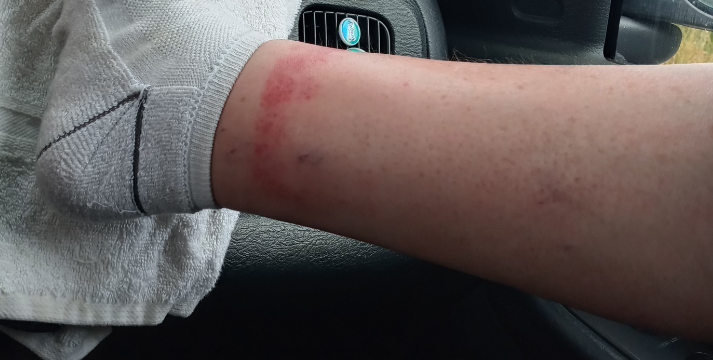Clinical context:
The affected area is the leg. The photo was captured at a distance.
Assessment:
On photographic review, Contact dermatitis and Allergic Contact Dermatitis were considered with similar weight; a more distant consideration is Stasis Dermatitis; less likely is Acute dermatitis, NOS; lower on the differential is Pigmented purpuric eruption.